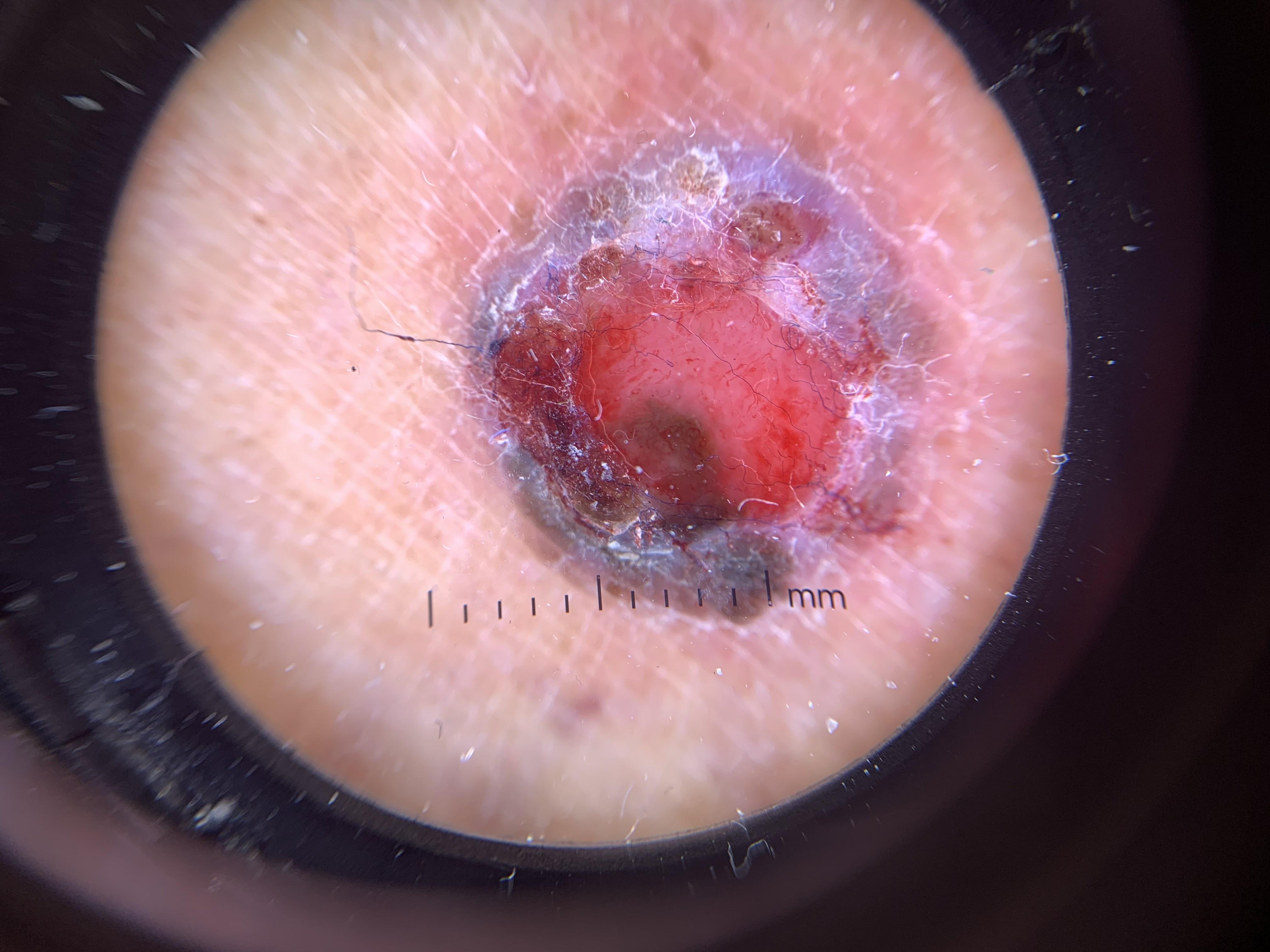A contact-polarized dermoscopy image of a skin lesion. A female patient roughly 80 years of age. FST III. Histopathologically confirmed as a malignant lesion — a melanoma.